Recorded as skin type III. A female subject roughly 20 years of age. A skin lesion imaged with contact-polarized dermoscopy.
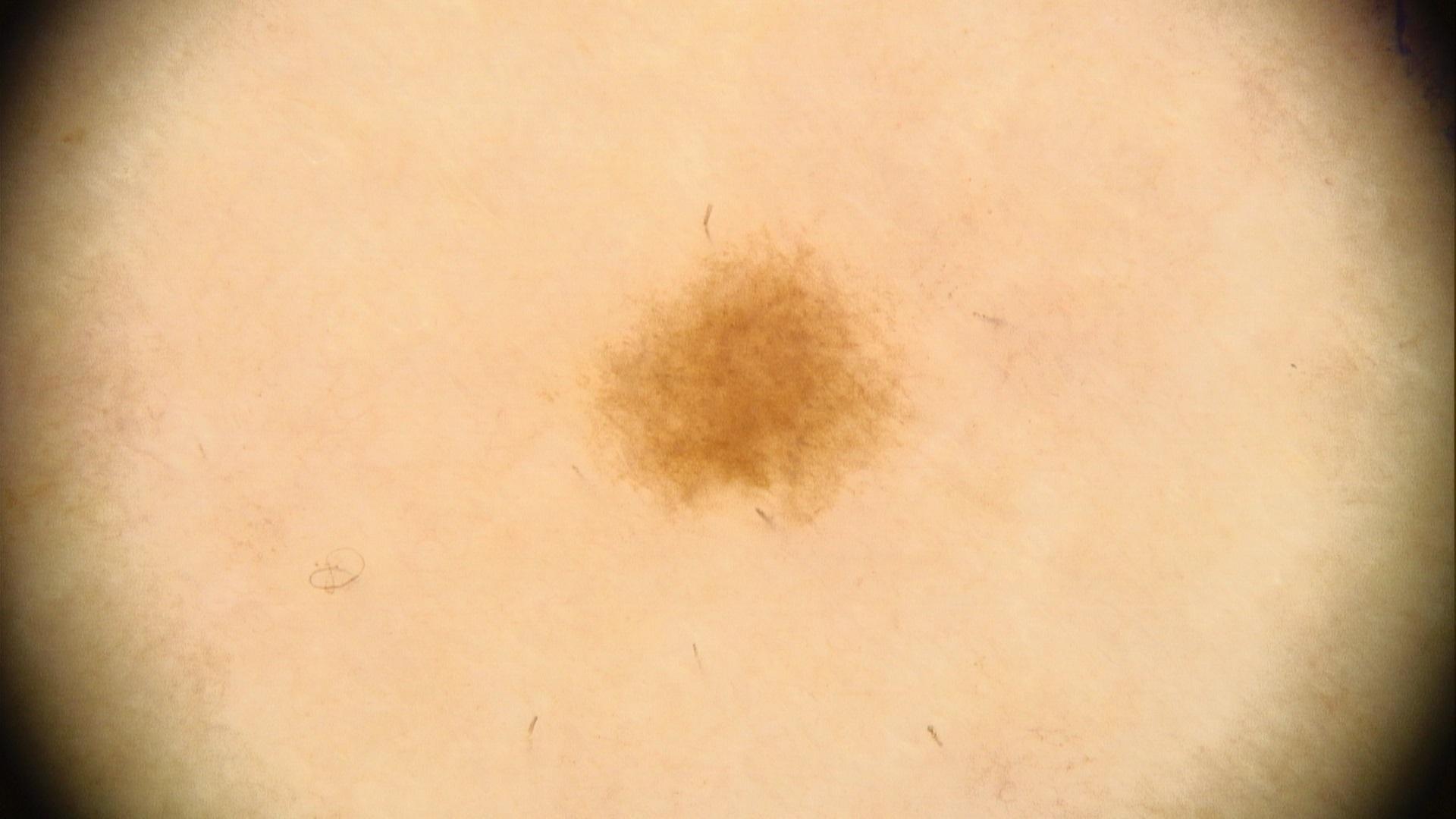impression = Nevus